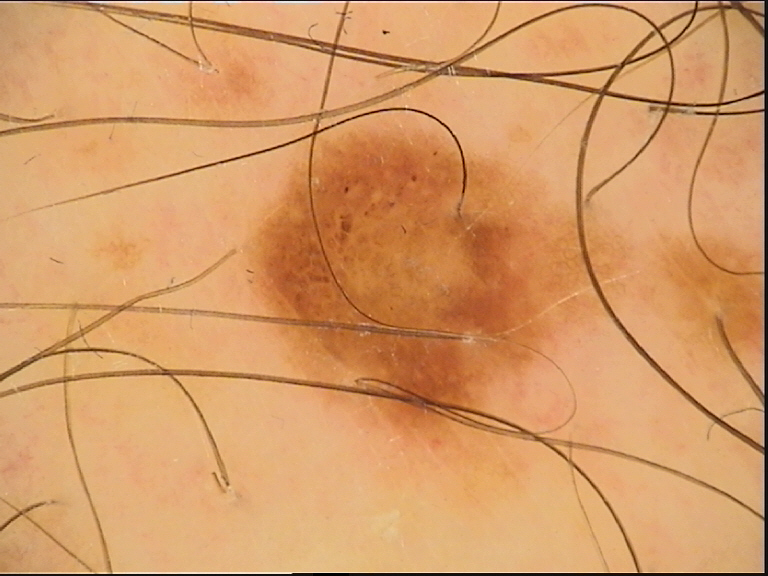A dermoscopic photograph of a skin lesion.
Consistent with a benign lesion — a dysplastic compound nevus.